The photograph is a close-up of the affected area, located on the head or neck, the patient notes the condition has been present for less than one week, the patient considered this a rash, the patient notes the lesion is raised or bumpy and rough or flaky: 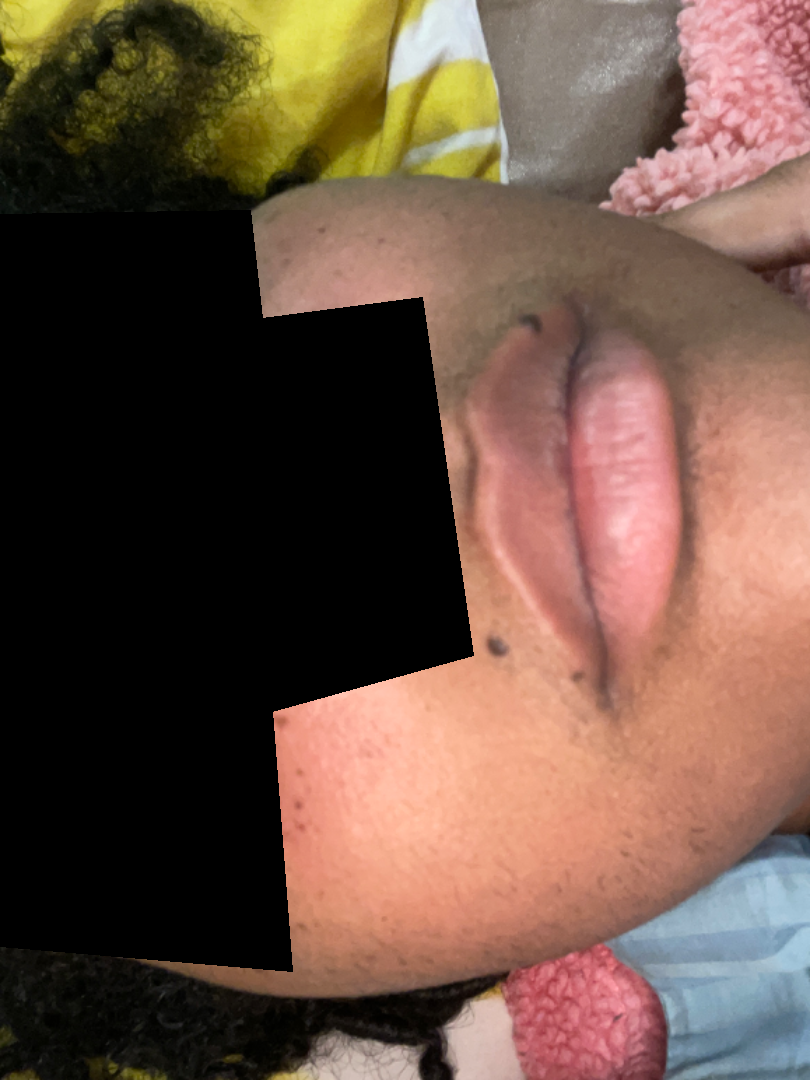No clear dermatological pathology was apparent in the photograph.